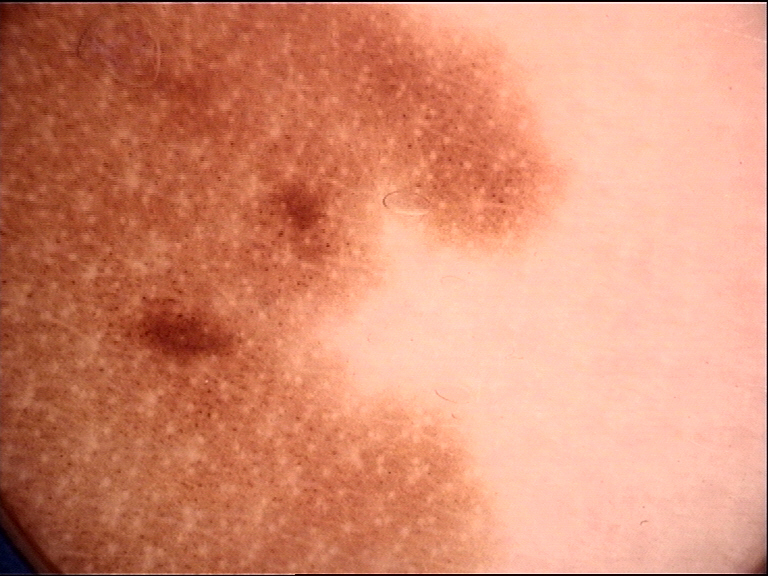Consistent with a congenital compound nevus.